Skin tone: FST IV; human graders estimated Monk Skin Tone 5 (US pool) or 4 (India pool) · located on the arm · the photograph is a close-up of the affected area.
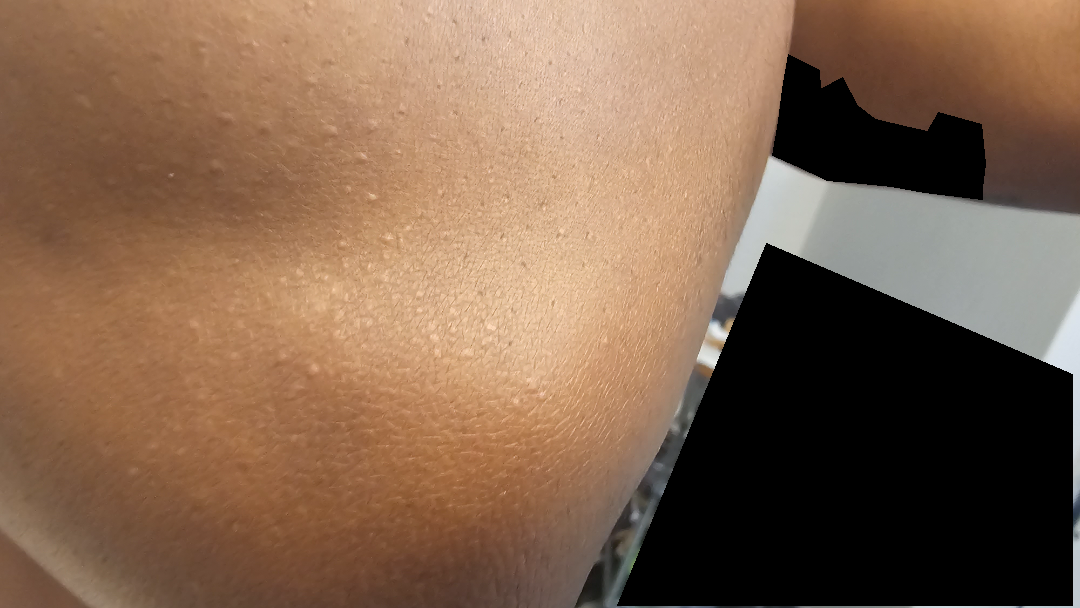Case summary:
• differential diagnosis · favoring Keratosis pilaris; with consideration of Milia; an alternative is Eczema